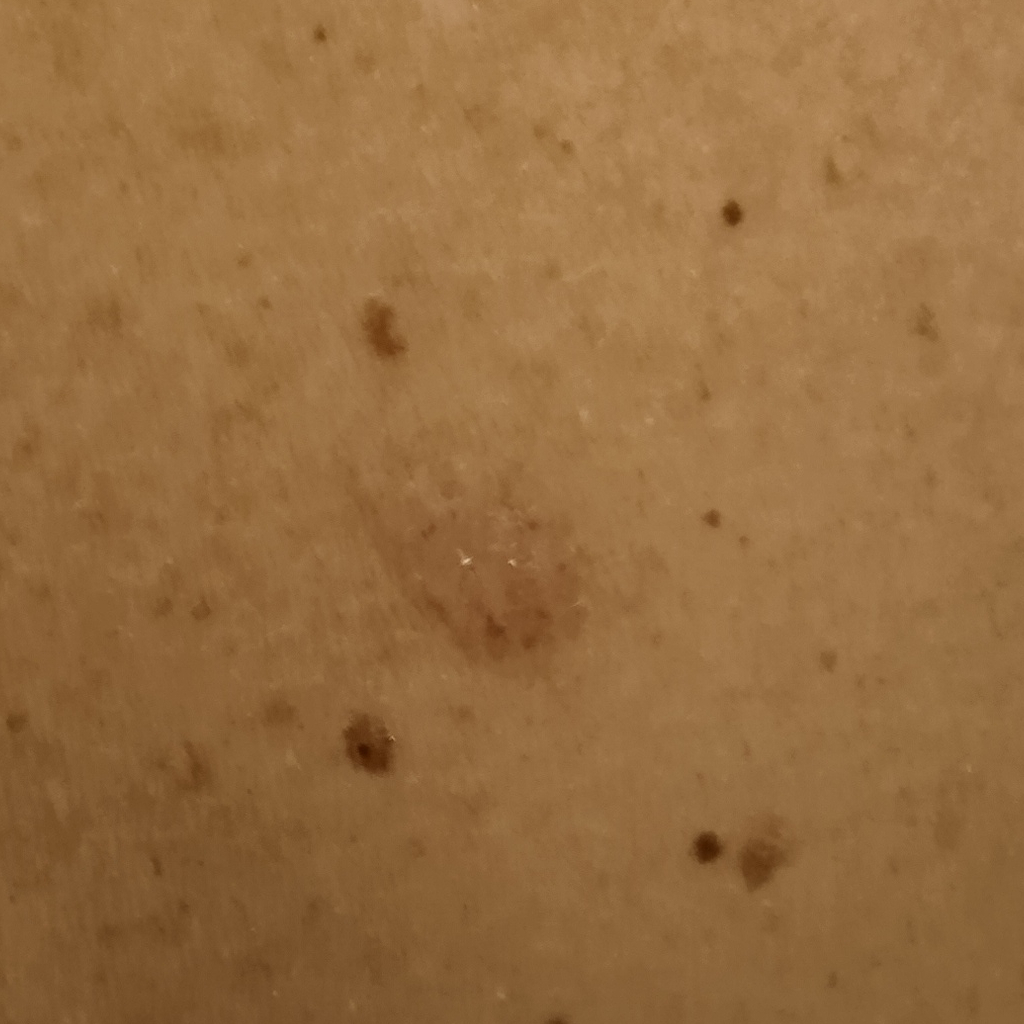Referred for assessment of suspected basal cell carcinoma.
A clinical photograph showing a skin lesion.
A female patient age 64.
Located on the back.
The lesion is about 9.8 mm across.
Histopathologically confirmed as a basal cell carcinoma, following excision, with a measured thickness of 1 mm.